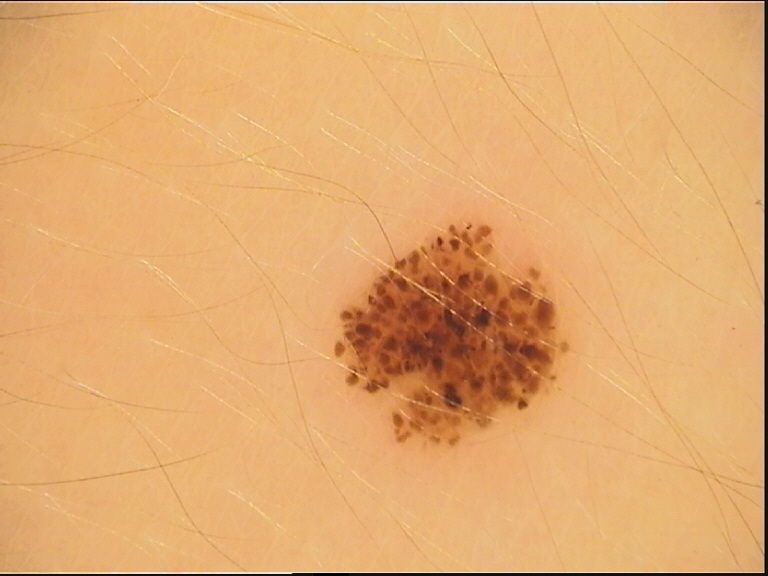A dermoscopic photograph of a skin lesion. Consistent with a banal lesion — a junctional nevus.